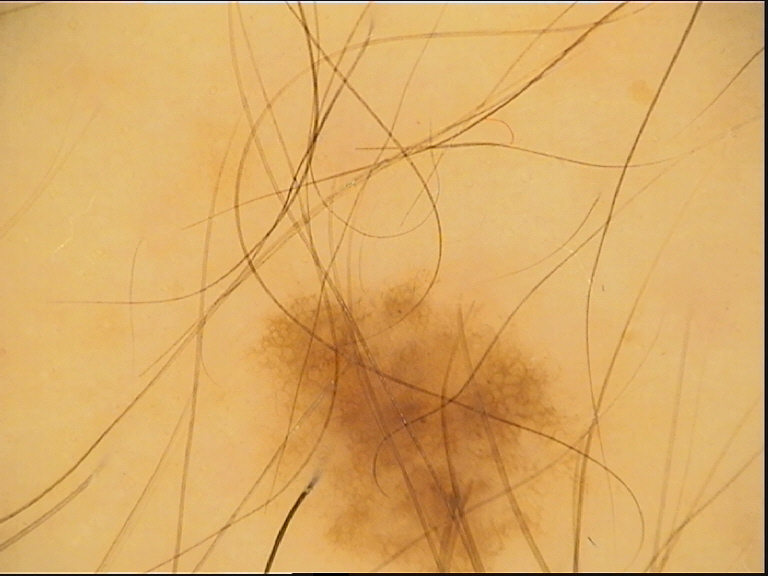Dermoscopy of a skin lesion. Classified as a dysplastic junctional nevus.